Referred for assessment of suspected basal cell carcinoma. A female subject age 60. Dermoscopy of a skin lesion. On a questionnaire the patient reported a personal history of cancer and a personal history of skin cancer. Few moles overall by the patient's own estimate. The patient says their skin tans without first burning:
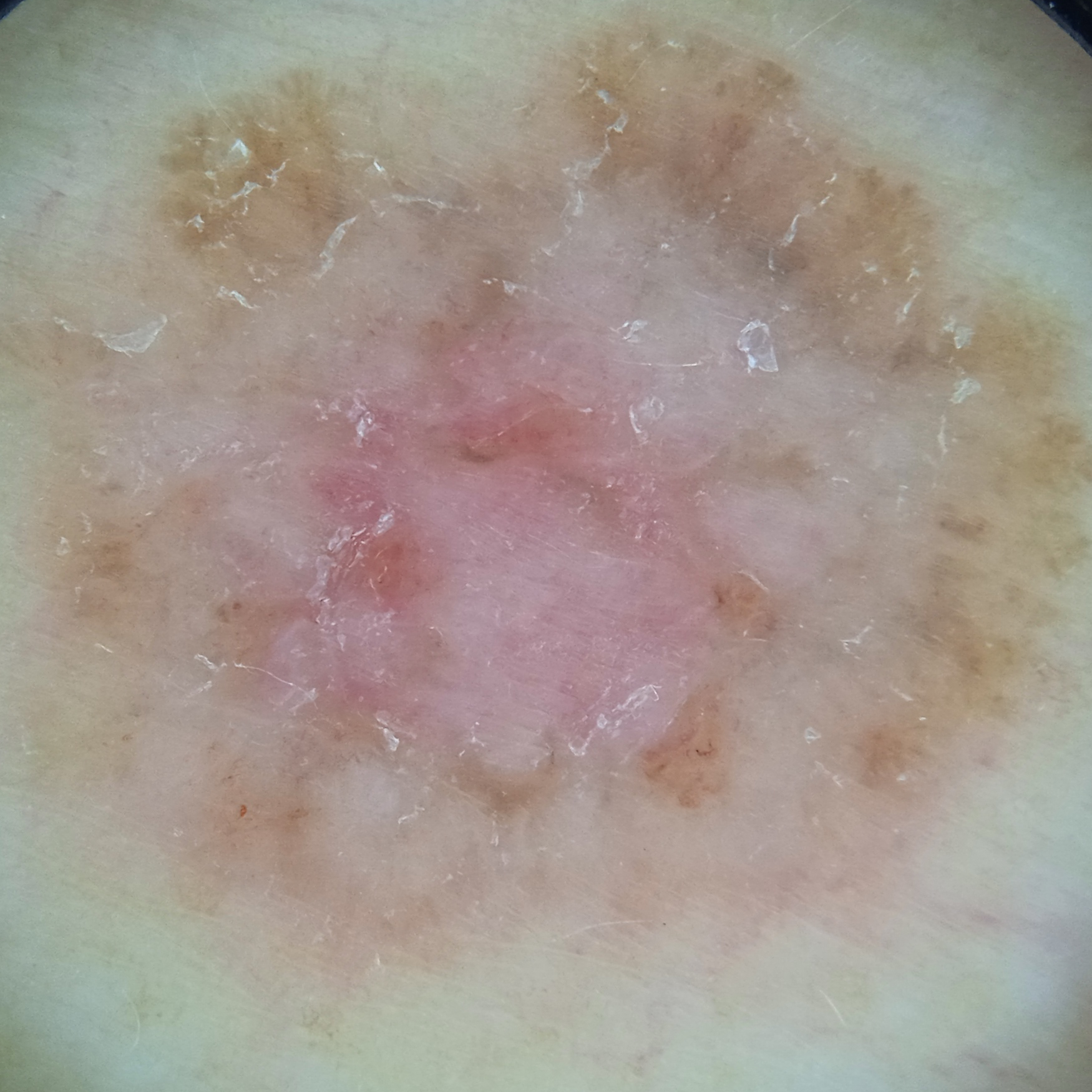body site=the torso
size=13.2 mm
diagnostic label=basal cell carcinoma (dermatologist consensus)